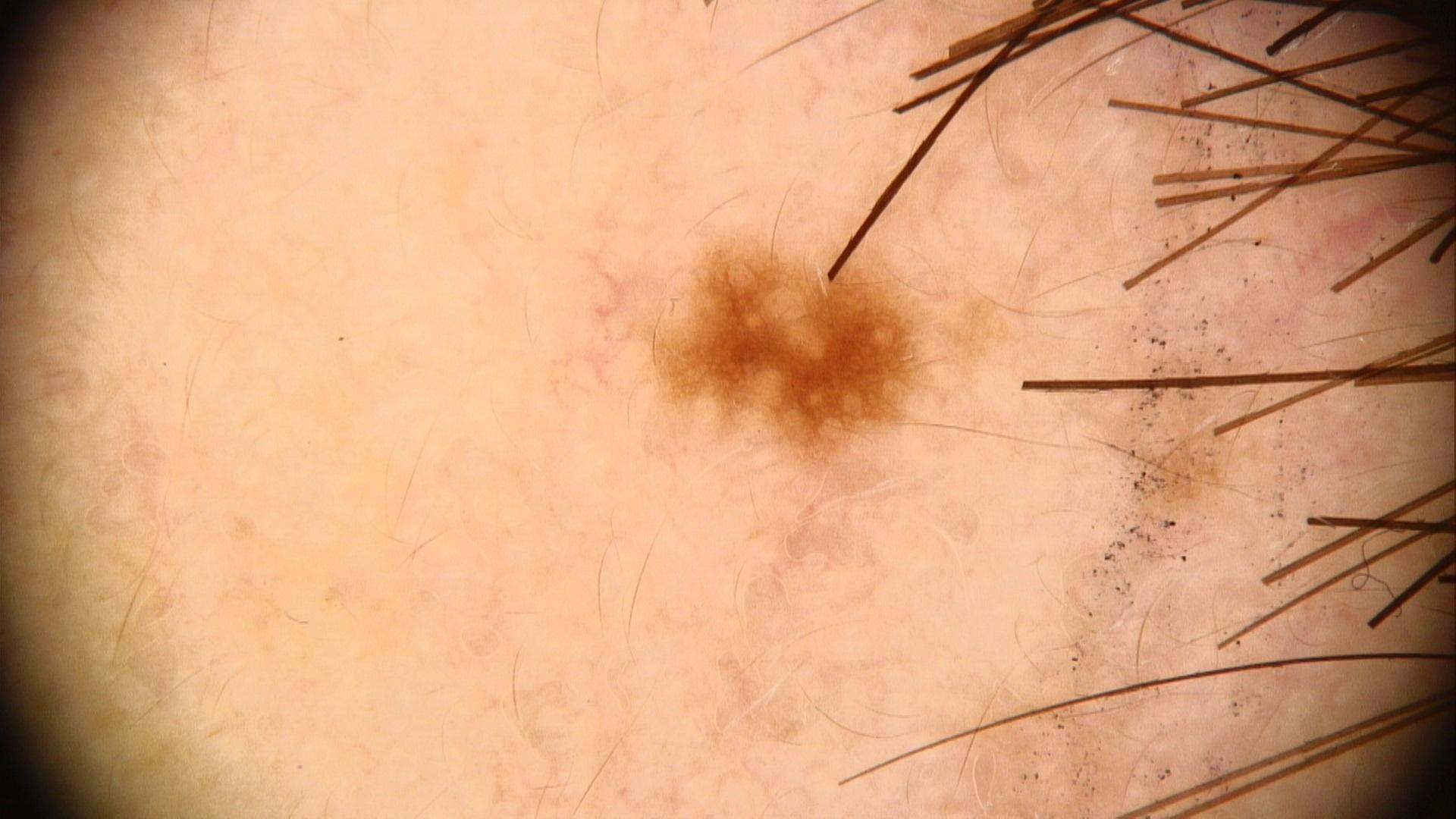The clinical impression was a nevus.